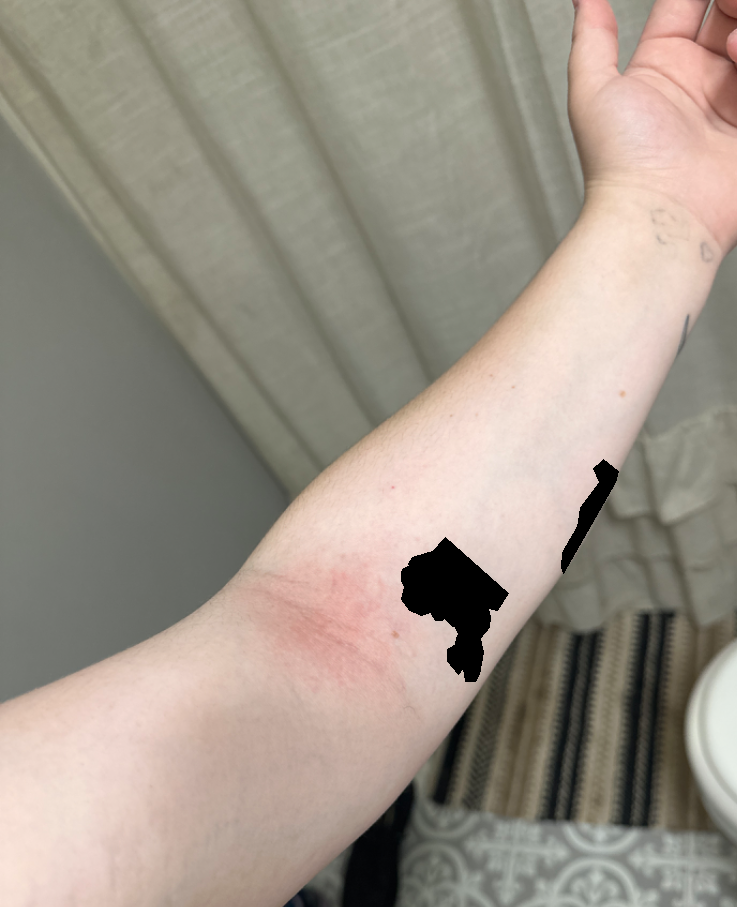Review: Most consistent with Eczema.